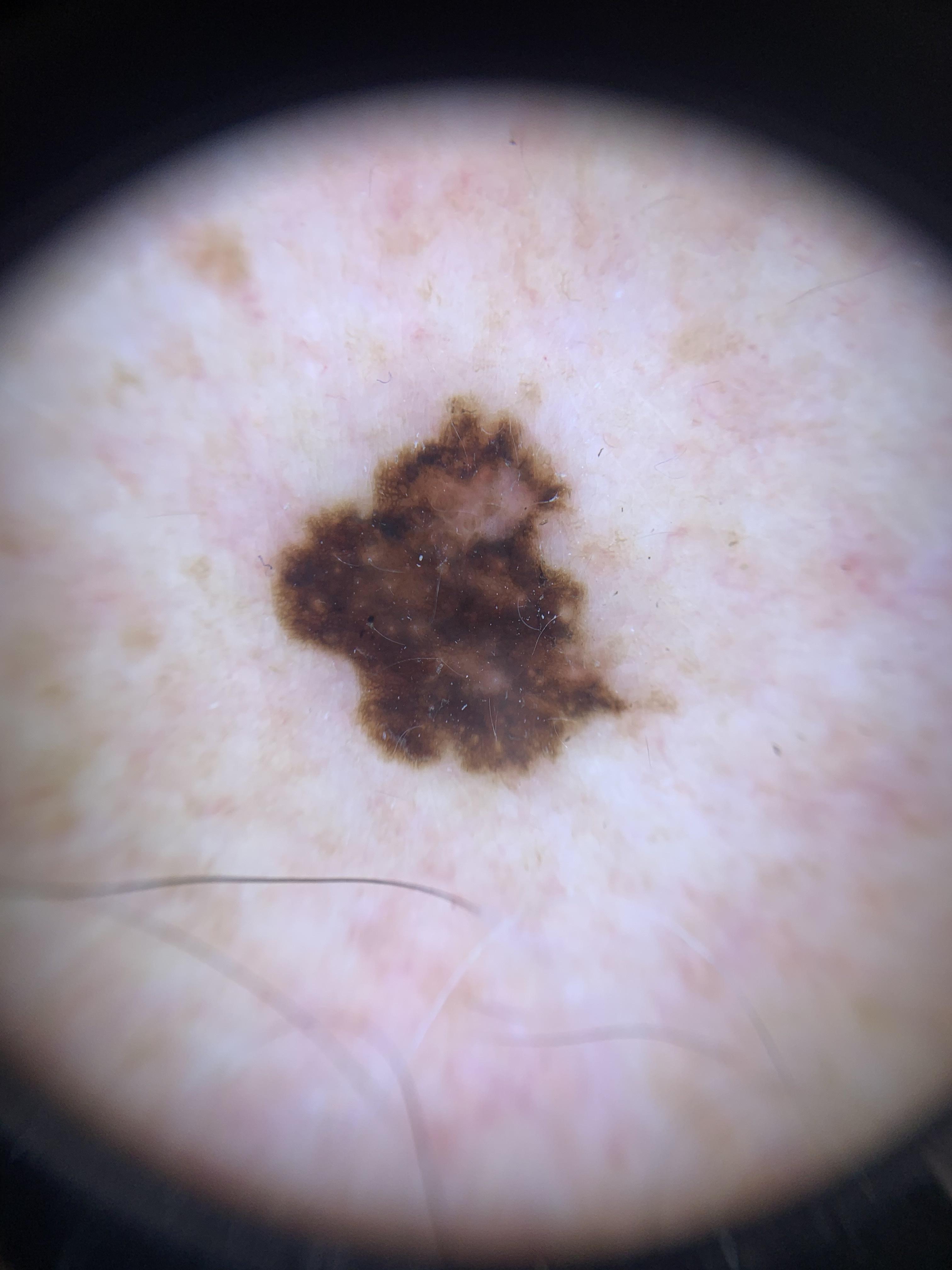Clinical context: Fitzpatrick skin type II. A male subject roughly 70 years of age. A dermatoscopic image of a skin lesion. Diagnosis: Histopathological examination showed a skin cancer — a melanoma.